A dermoscopy image of a single skin lesion: 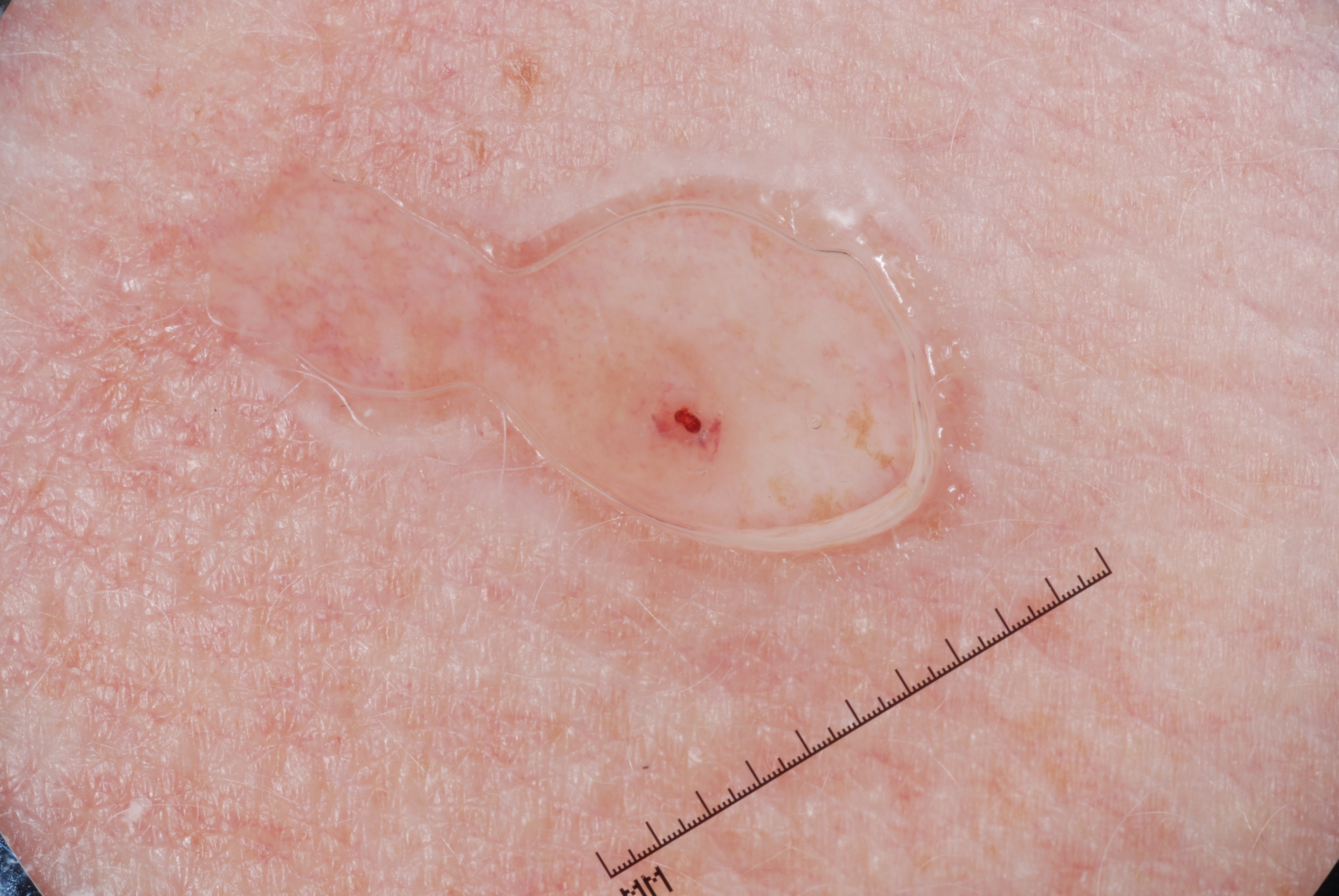In (x1, y1, x2, y2) order, the visible lesion spans 514, 294, 759, 508.
Expert review diagnosed this as a melanocytic nevus, a benign skin lesion.